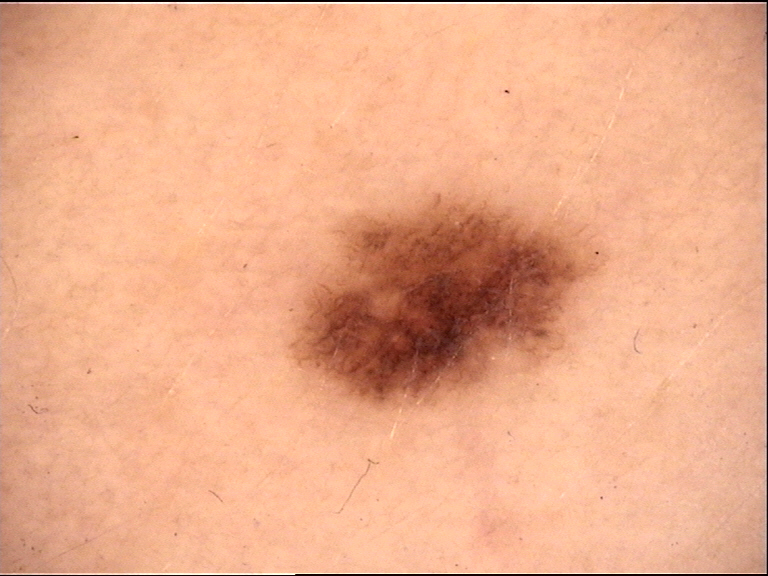Dermoscopy of a skin lesion.
Classified as a benign lesion — a dysplastic junctional nevus.